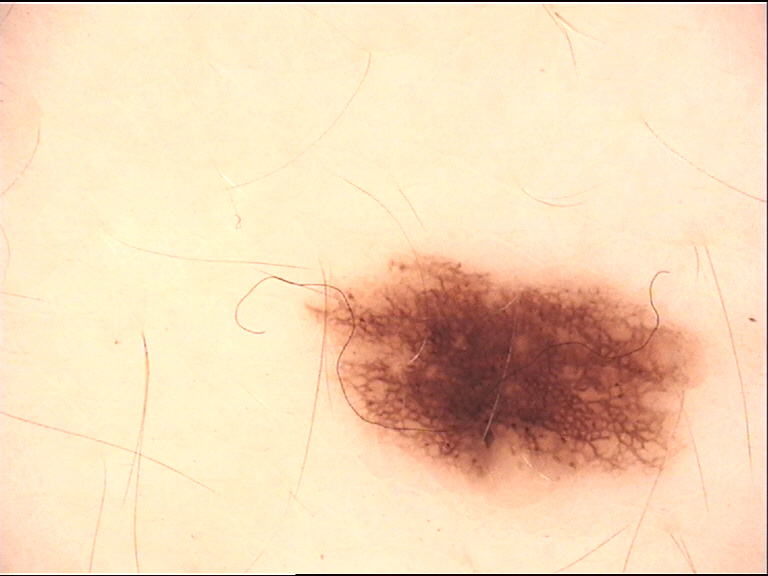A dermoscopy image of a single skin lesion. Labeled as a benign lesion — a dysplastic junctional nevus.